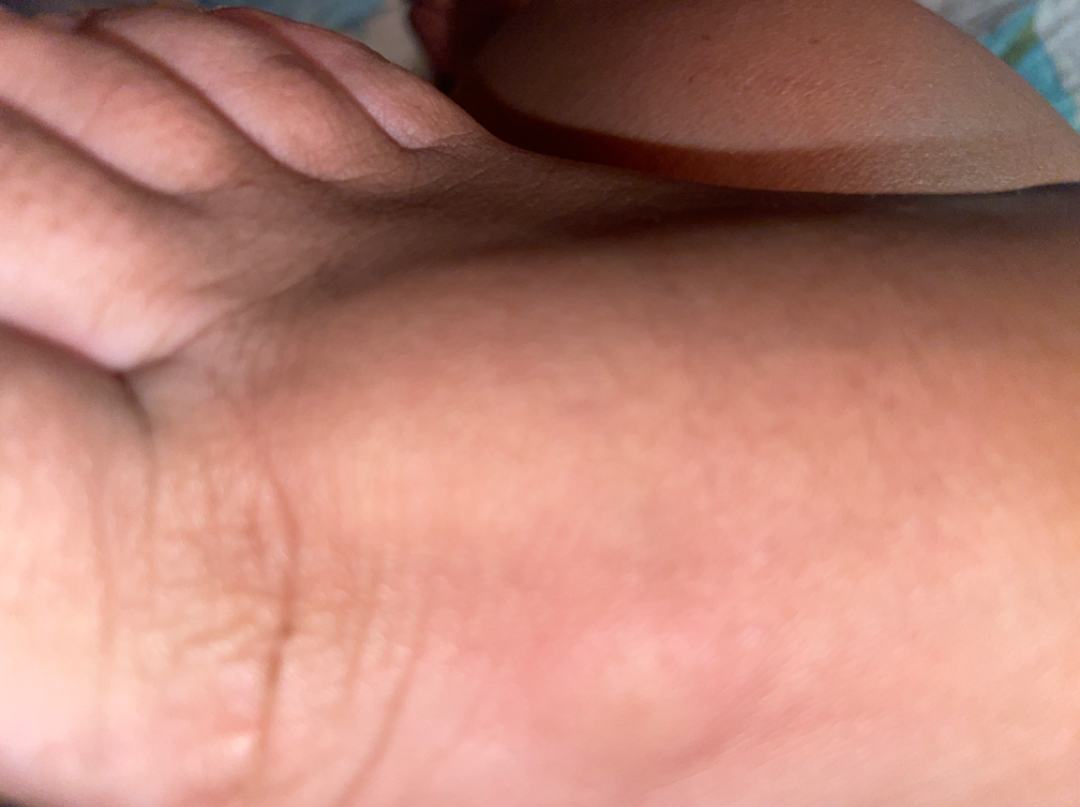Assessment:
The condition could not be reliably identified from the image.
Clinical context:
Present for less than one week. No relevant systemic symptoms. This image was taken at an angle. The lesion is described as fluid-filled and raised or bumpy. Reported lesion symptoms include enlargement, burning, itching and bothersome appearance. Self-categorized by the patient as a nail problem. The affected area is the arm, palm, head or neck, back of the hand, leg and sole of the foot.